A dermoscopy image of a single skin lesion: 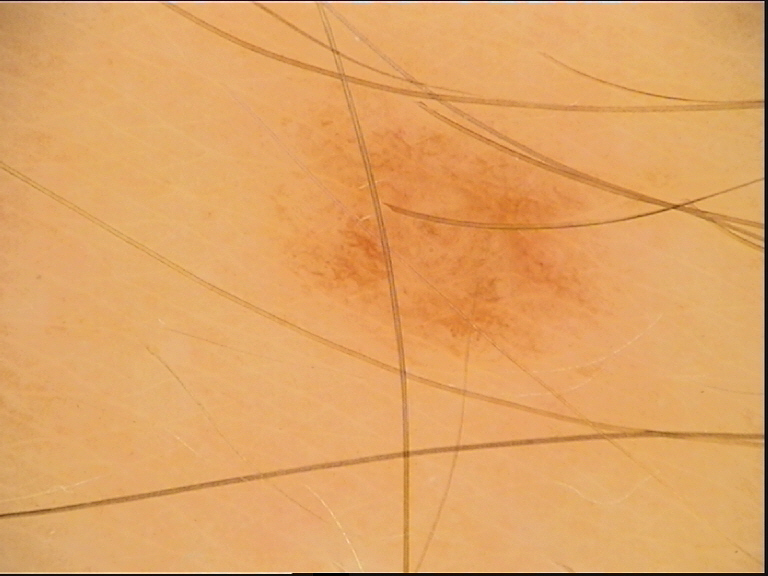Q: What is this lesion?
A: dysplastic junctional nevus (expert consensus)